A dermoscopy image of a single skin lesion.
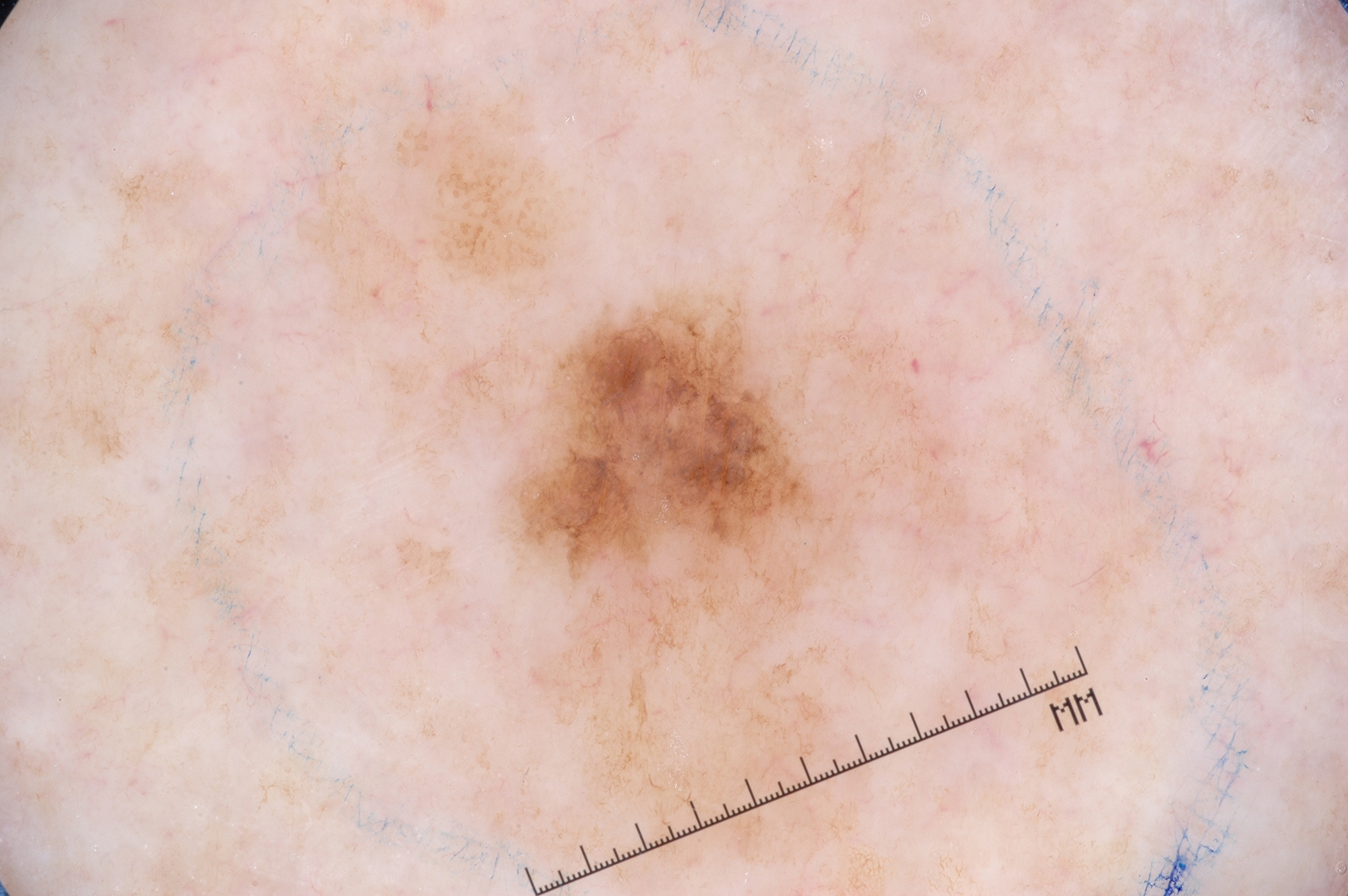A mid-sized lesion within the field. With coordinates (x1, y1, x2, y2), the lesion's extent is 358 274 983 887. Dermoscopic assessment notes no pigment network, milia-like cysts, streaks, or negative network. Histopathological examination showed a melanoma, a malignant lesion.